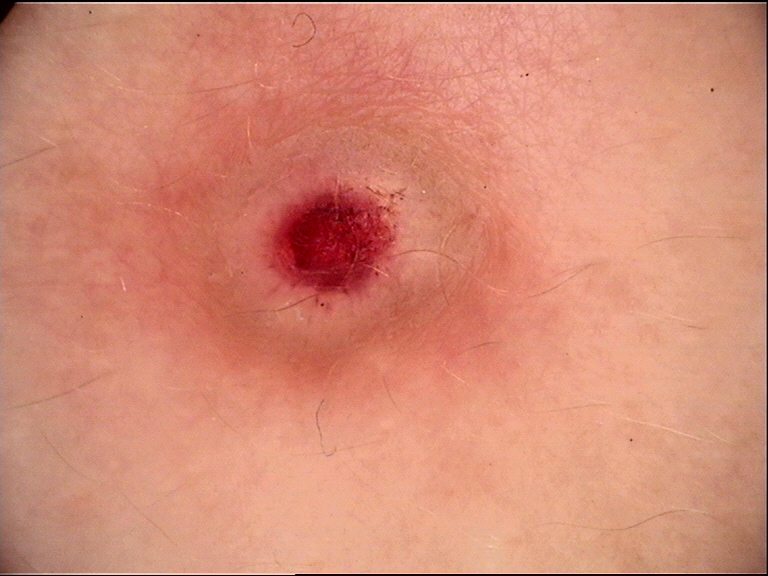{
  "diagnosis": {
    "name": "dermatofibroma",
    "code": "df",
    "malignancy": "benign",
    "super_class": "non-melanocytic",
    "confirmation": "expert consensus"
  }
}